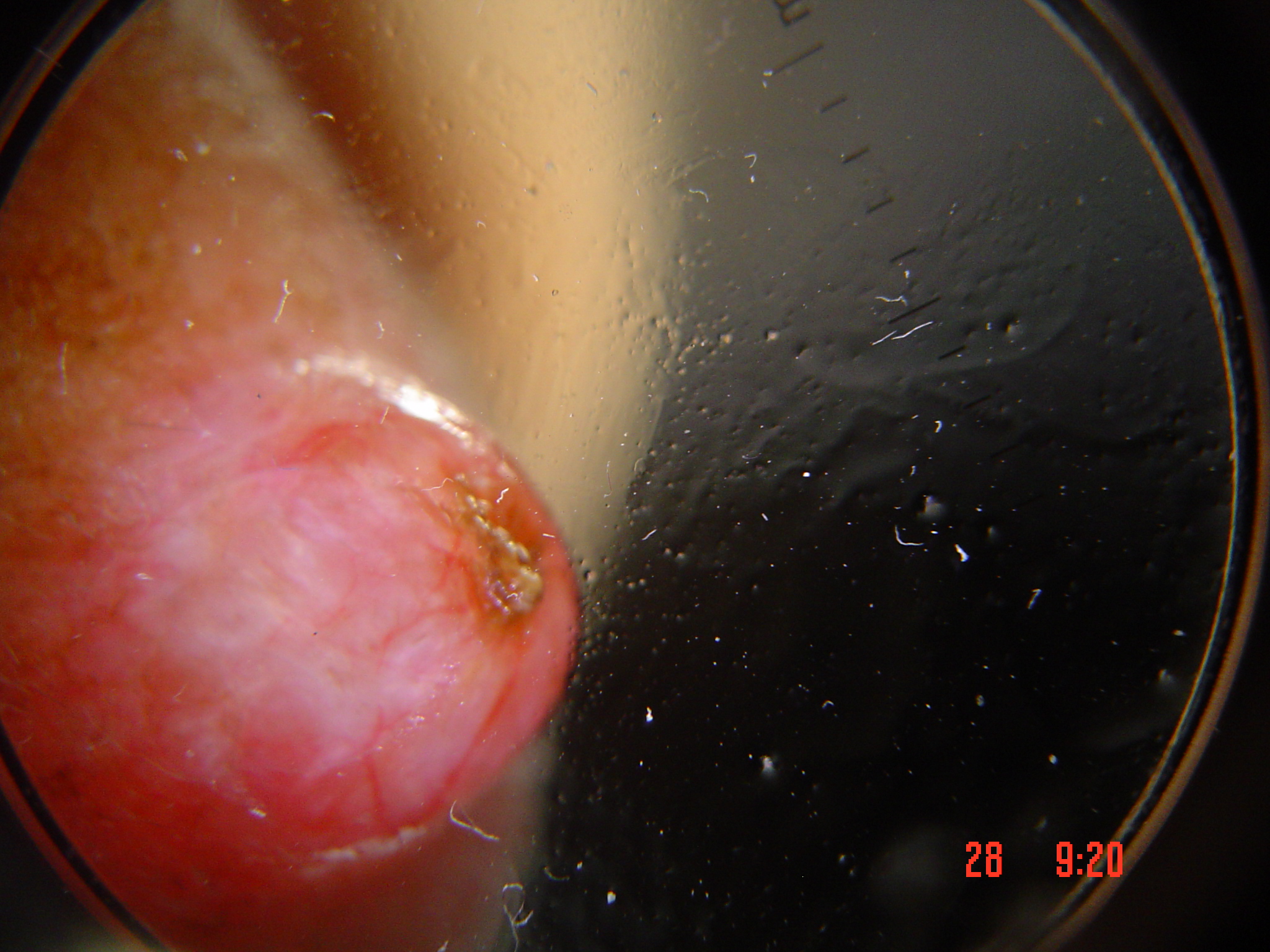diagnostic label — basal cell carcinoma (biopsy-proven).